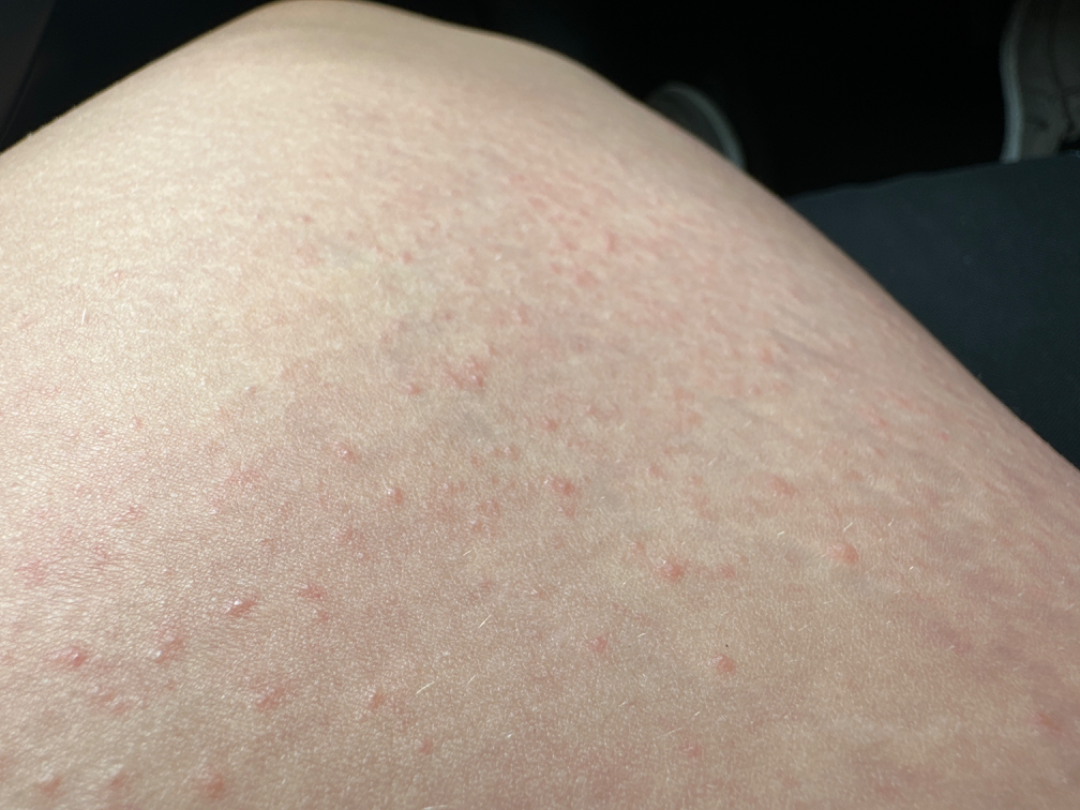assessment: ungradable on photographic review | image framing: at an angle.